A dermoscopic close-up of a skin lesion. A female patient roughly 20 years of age:
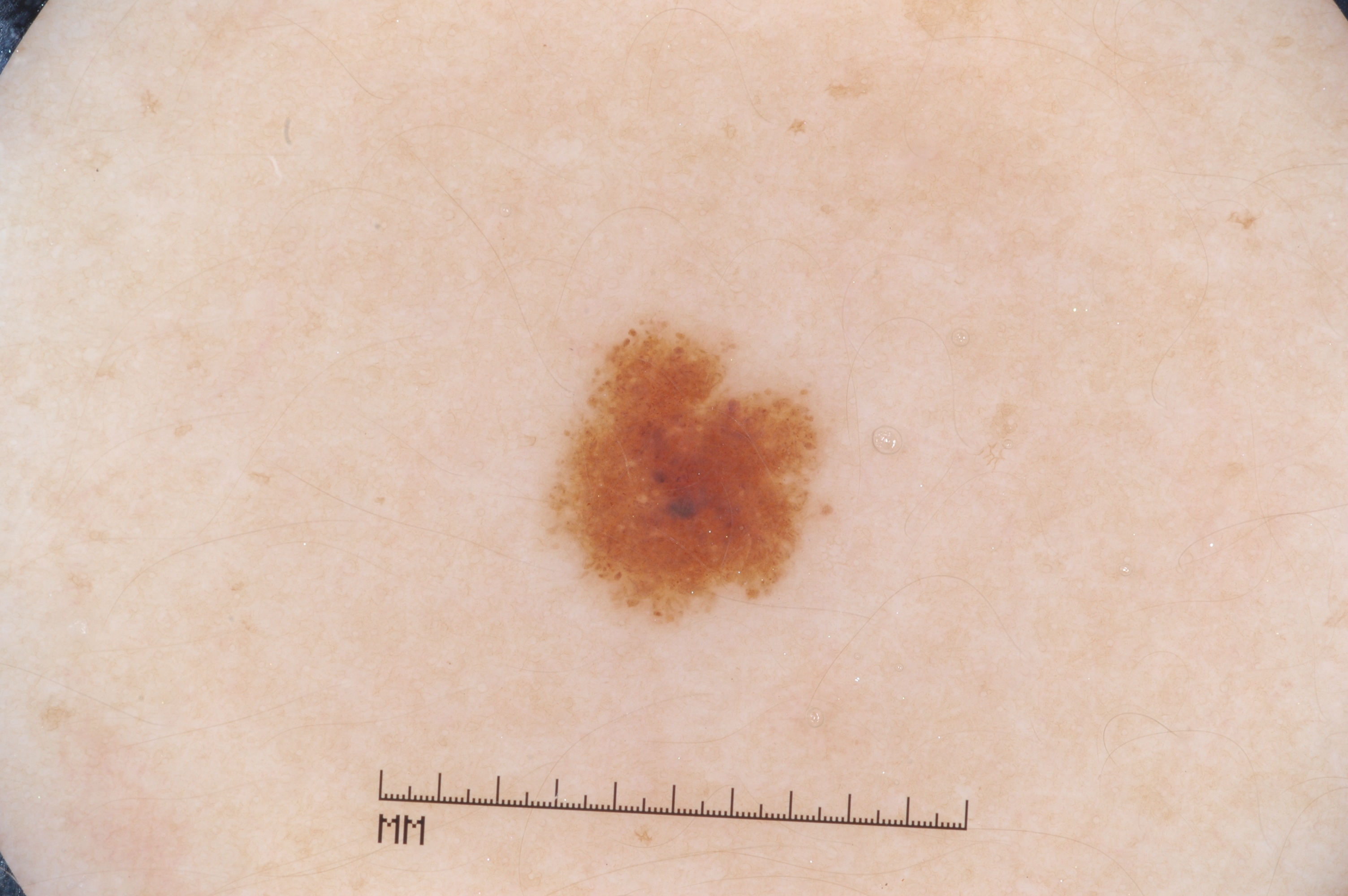| field | value |
|---|---|
| size | ~5% of the field |
| features | milia-like cysts; absent: pigment network, streaks, and negative network |
| lesion location | left=558, top=329, right=822, bottom=616 |
| impression | a melanocytic nevus |